The contributor is 60–69, male; the photo was captured at an angle; located on the leg:
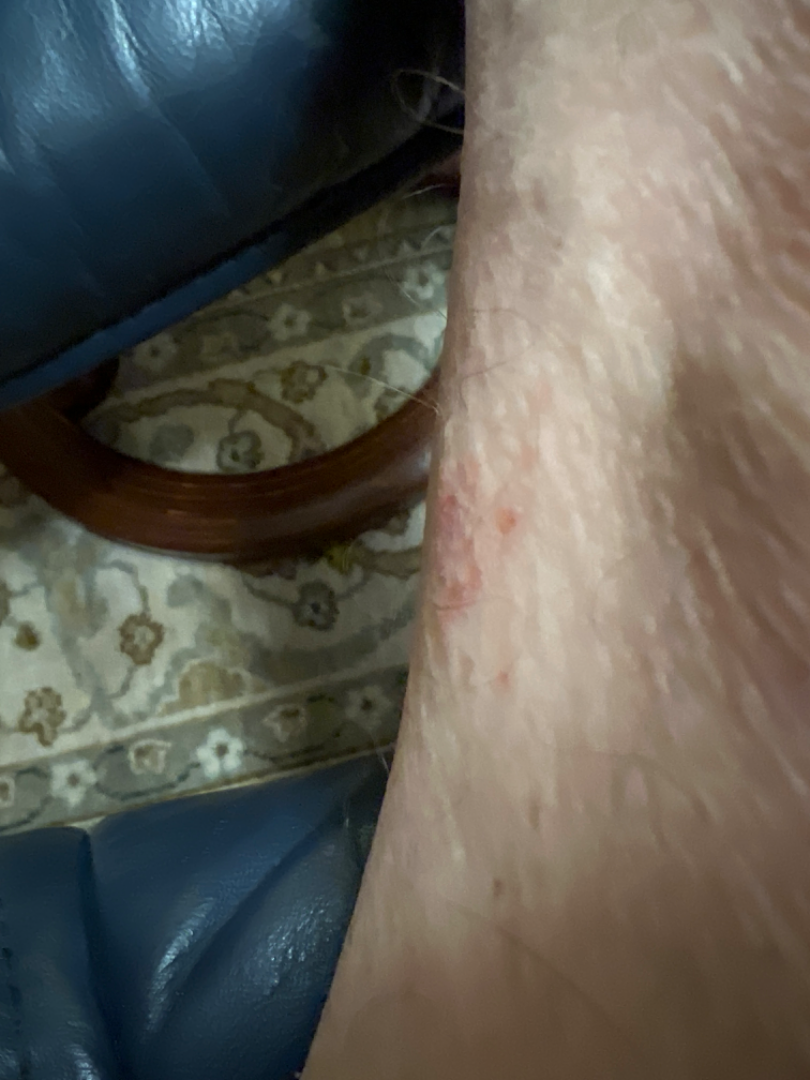Impression: On teledermatology review, most consistent with Eczema.